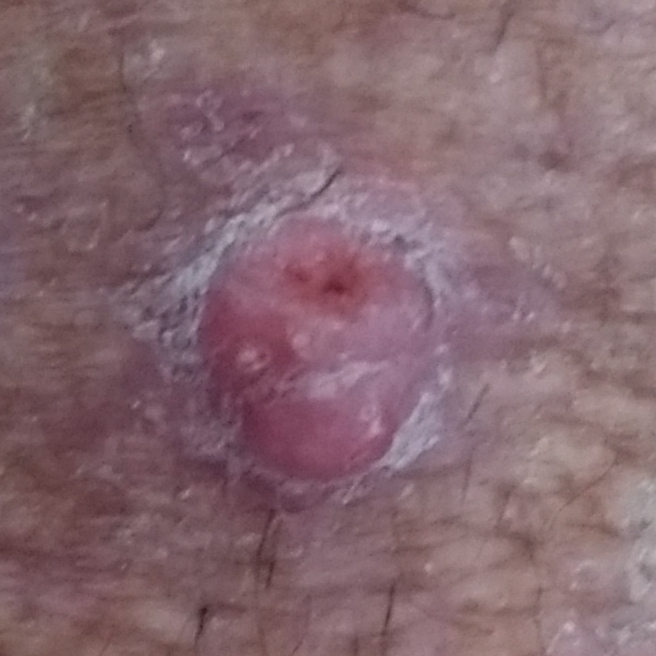Q: What is this lesion?
A: squamous cell carcinoma (biopsy-proven)